Few moles overall by the patient's own estimate. The patient says their skin tans without first burning. A male patient 64 years of age. Referred for assessment of suspected seborrheic keratosis. A clinical close-up of a skin lesion — 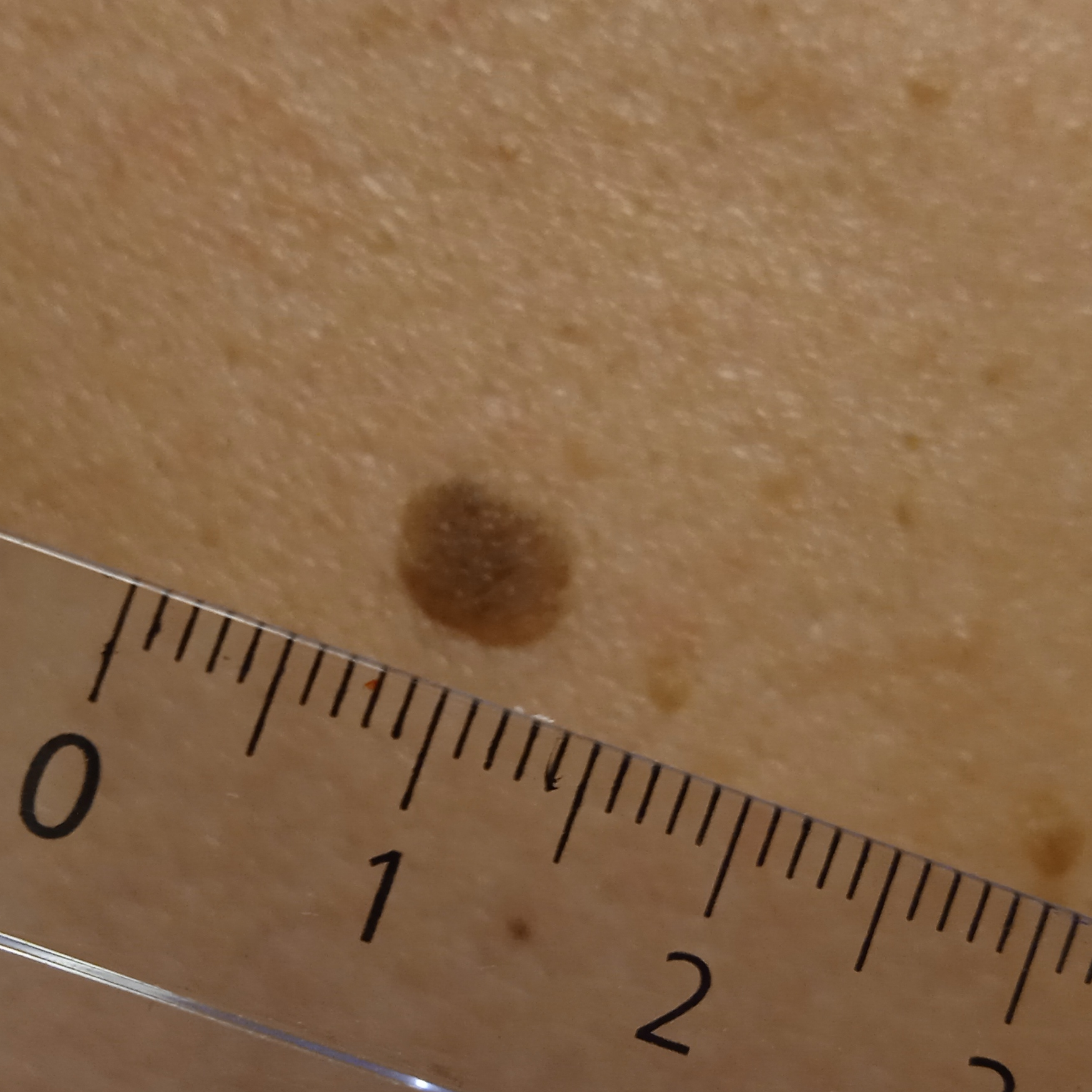site: the back; assessment: seborrheic keratosis (dermatologist consensus).